The subject is a female aged 38 to 42, this is a dermoscopic photograph of a skin lesion:
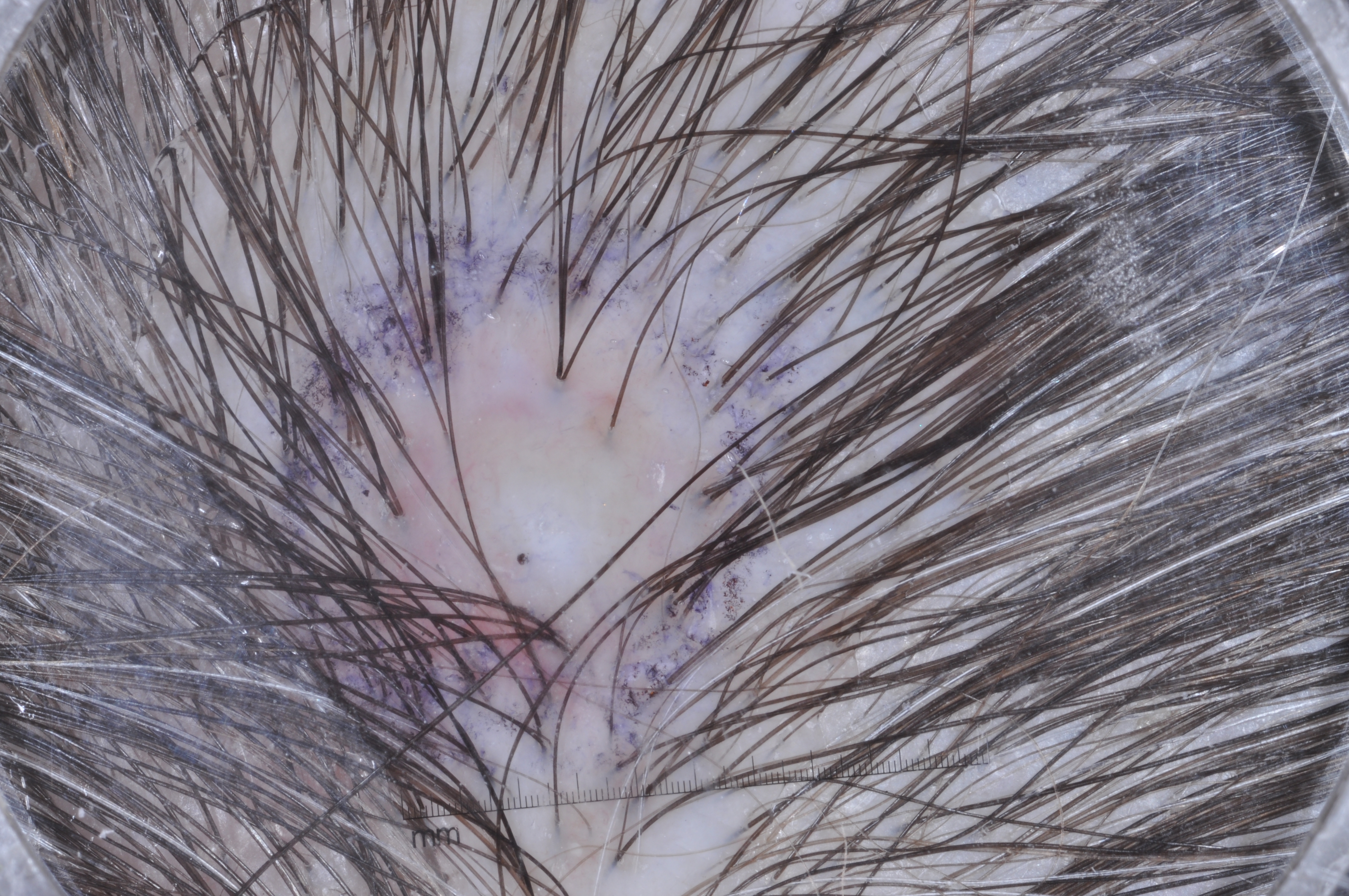lesion_extent:
  approx_field_fraction_pct: 12
dermoscopic_features:
  present: []
  absent:
    - pigment network
    - milia-like cysts
    - negative network
    - streaks
lesion_location:
  bbox_xyxy:
    - 307
    - 286
    - 740
    - 747
diagnosis:
  name: melanocytic nevus
  malignancy: benign
  lineage: melanocytic
  provenance: clinical